A dermatoscopic image of a skin lesion.
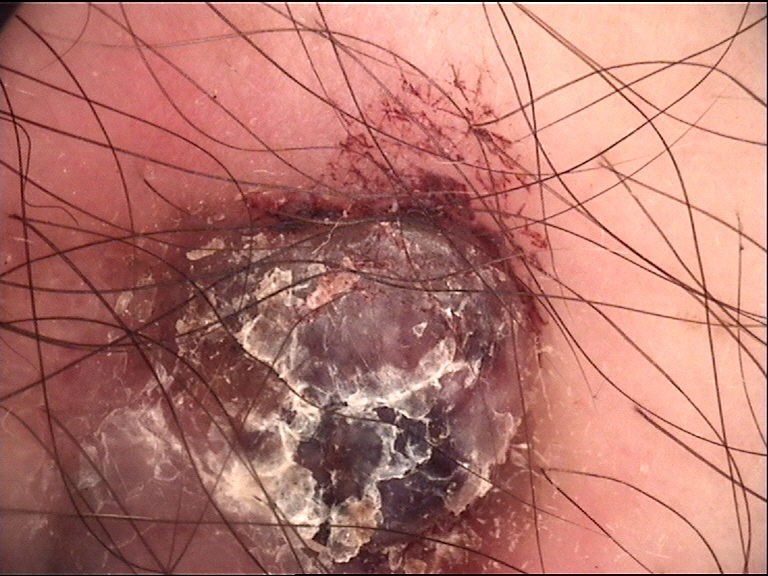Q: What is the diagnosis?
A: melanoma (biopsy-proven)